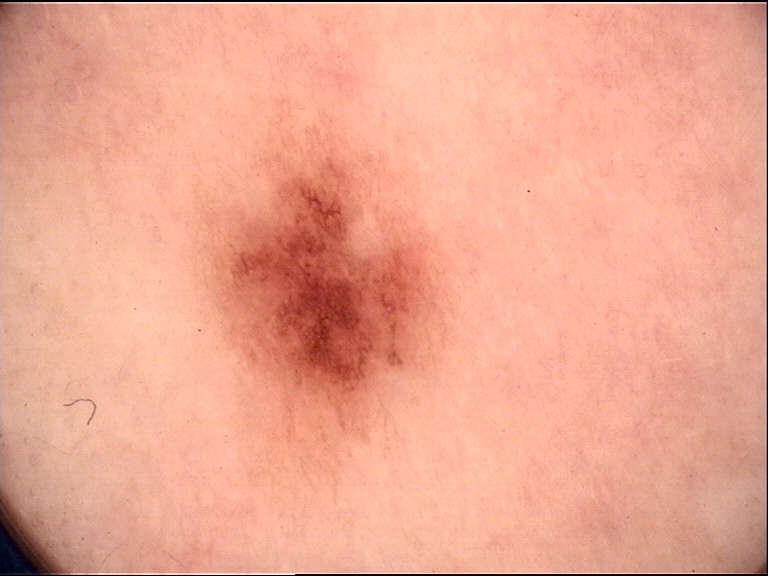A skin lesion imaged with a dermatoscope. Consistent with a dysplastic junctional nevus.